An image taken at an angle, the leg and top or side of the foot are involved:
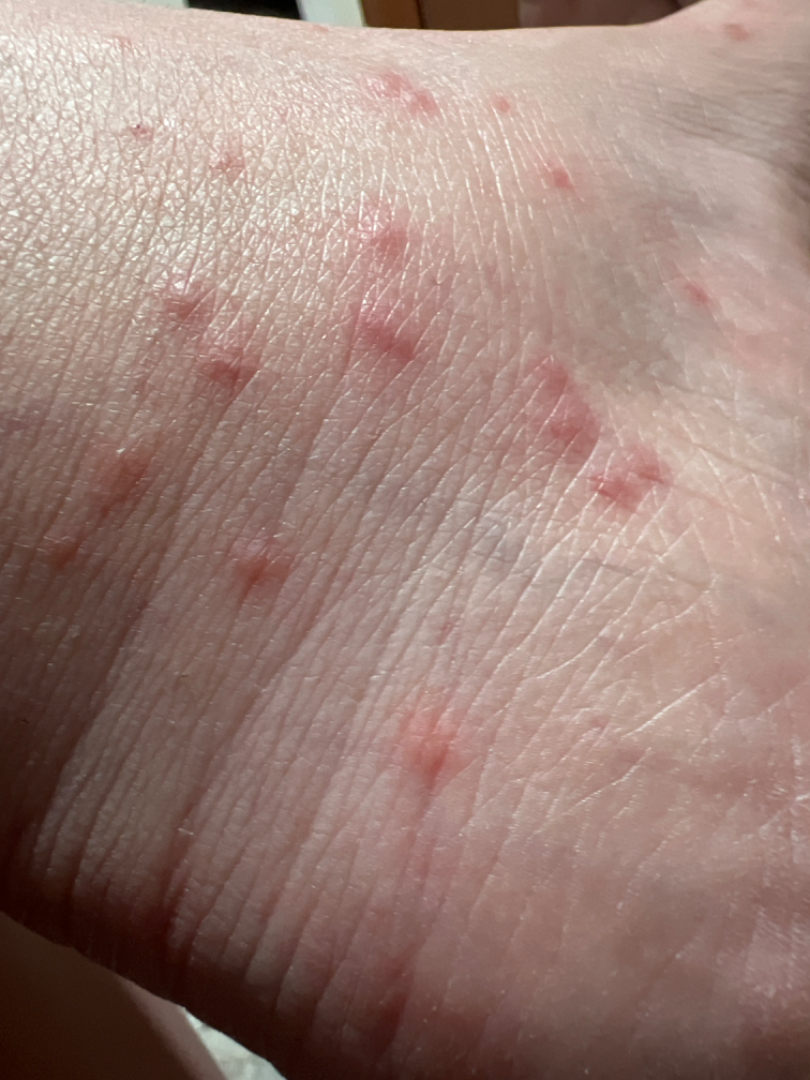other reported symptoms=none reported | patient's own categorization=a rash | lesion texture=raised or bumpy | reported symptoms=itching | symptom duration=less than one week | differential diagnosis=favoring Scabies; an alternative is Insect Bite; less probable is Eczema.